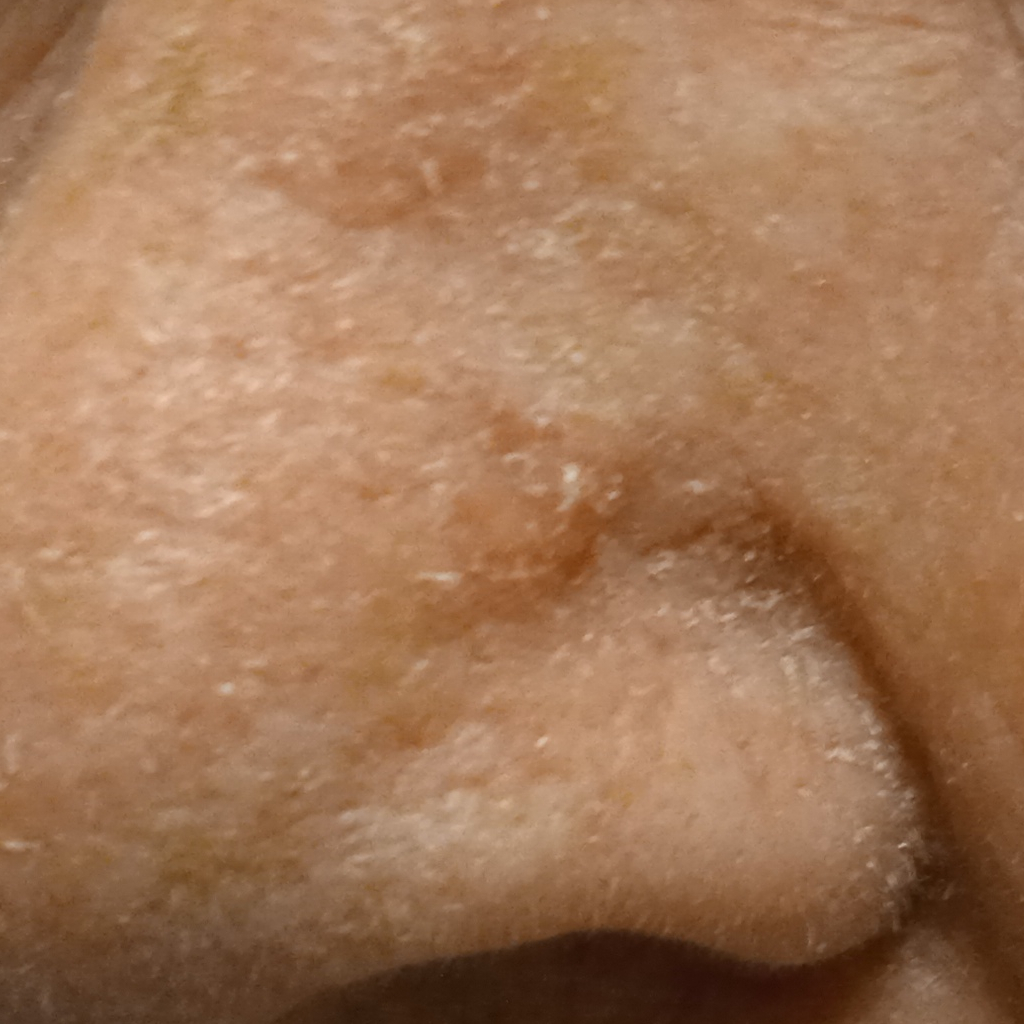| feature | finding |
|---|---|
| subject | female, 92 years of age |
| image type | clinical photo |
| clinical context | research study (no referral diagnosis) |
| location | the face |
| lesion size | 7 mm |
| diagnosis | basal cell carcinoma (dermatologist consensus) |